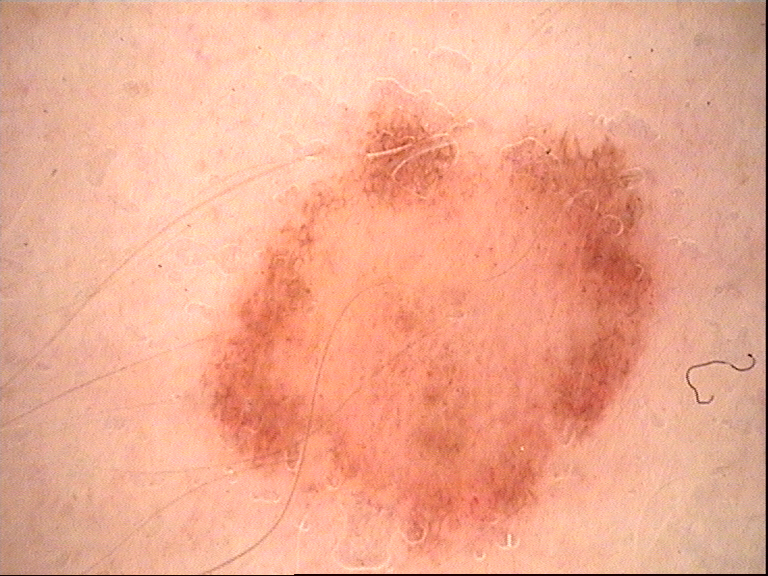A dermatoscopic image of a skin lesion.
The architecture is that of a banal lesion.
The diagnosis was a compound nevus.